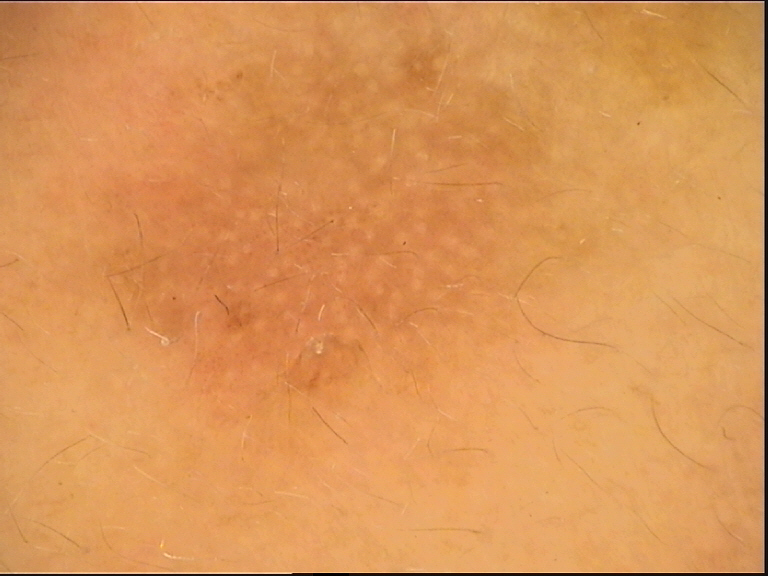imaging: dermatoscopy; assessment: dysplastic junctional nevus (expert consensus).